Located on the head or neck. This is a close-up image. Male contributor, age 18–29.
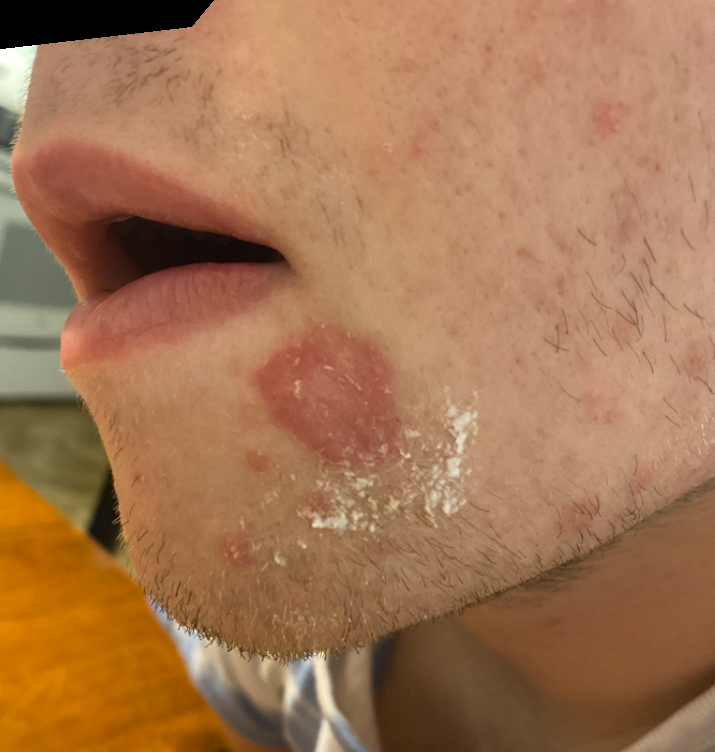Background: Symptoms reported: bothersome appearance and pain. Reported duration is less than one week. The lesion is described as raised or bumpy. Findings: Impetigo (possible); Allergic Contact Dermatitis (possible); Irritant Contact Dermatitis (possible).